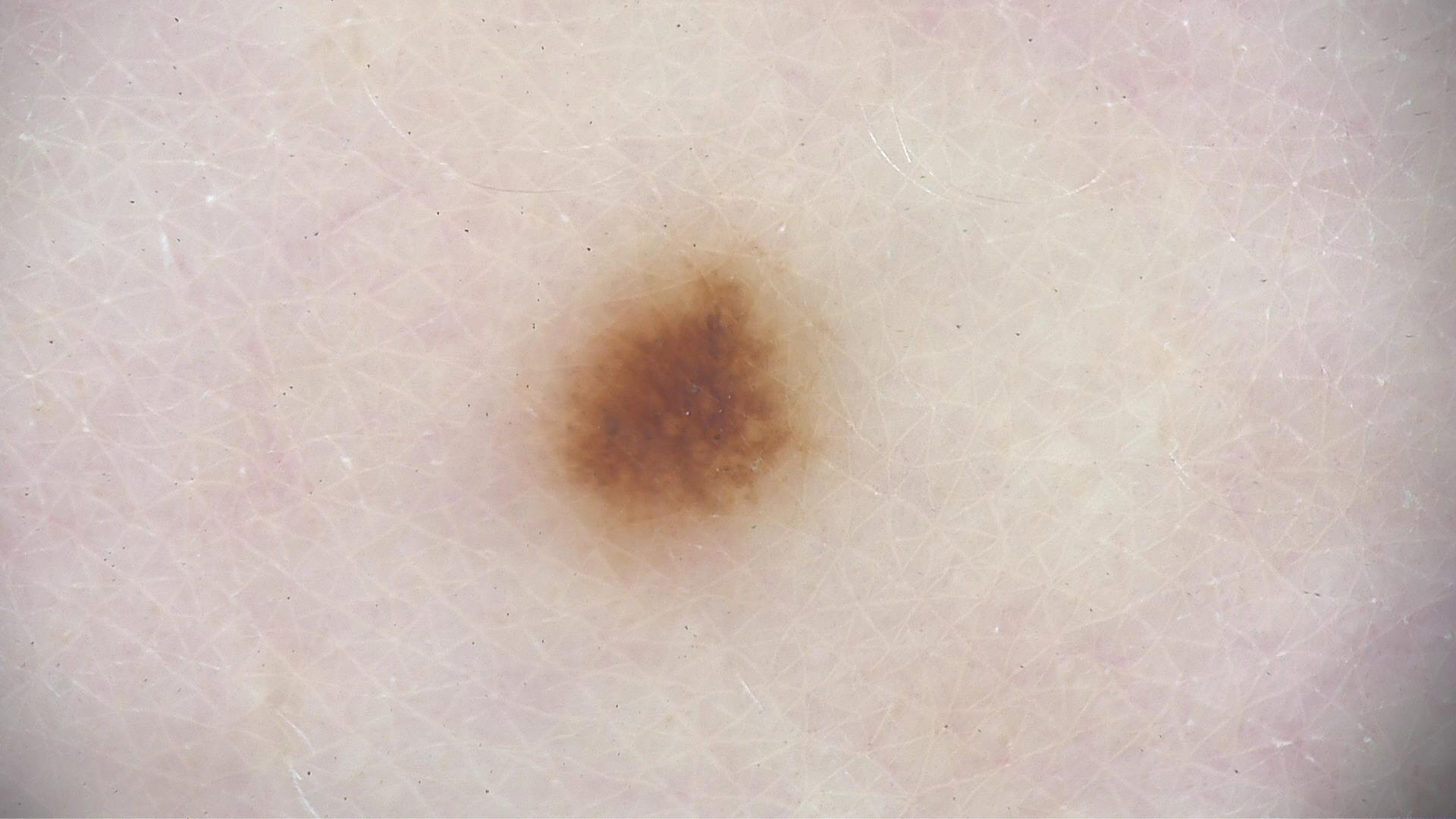Consistent with a benign lesion — a dysplastic junctional nevus.